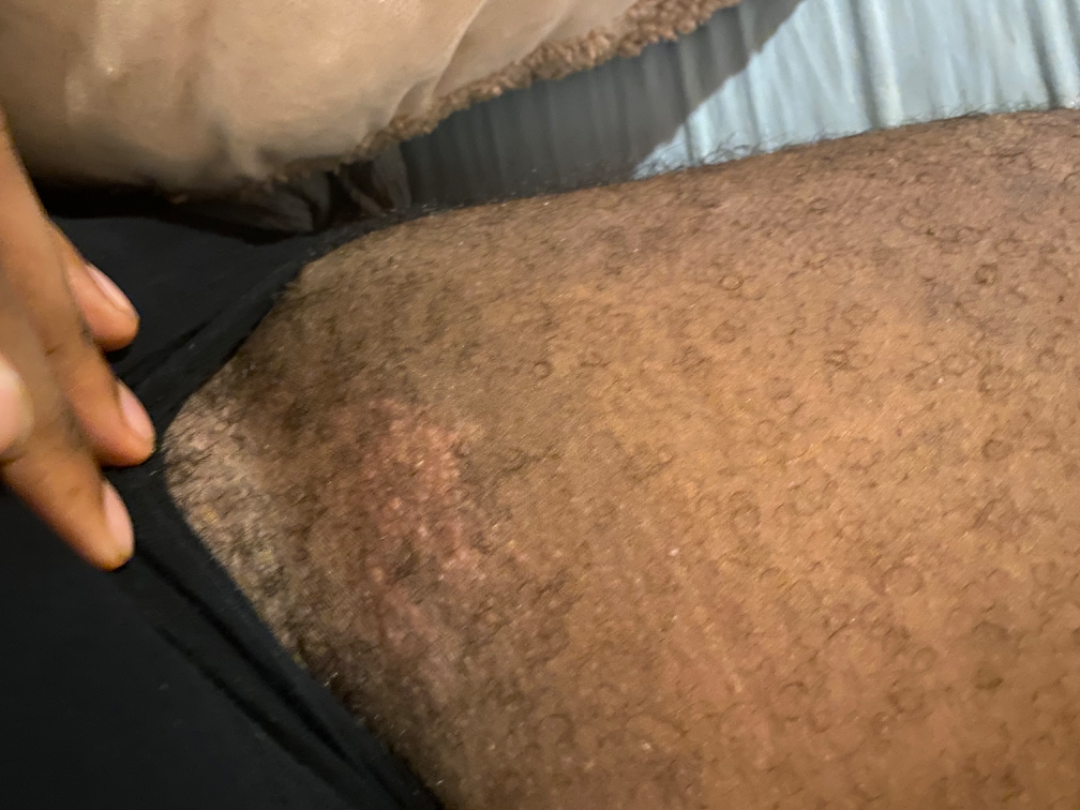Findings: The skin findings could not be characterized from the image. Background: An image taken at an angle.